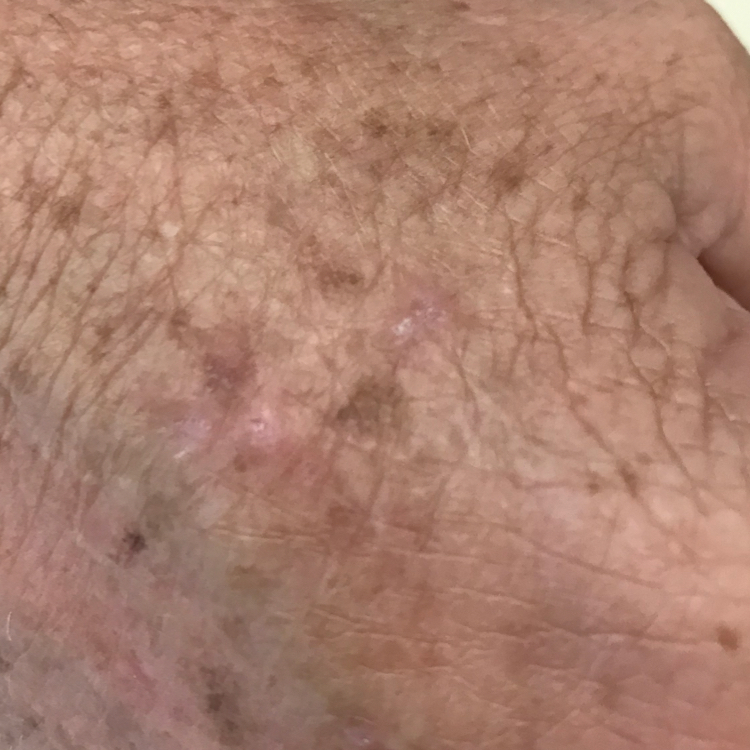Q: What is the imaging modality?
A: clinical photo
Q: Patient demographics?
A: age 48
Q: Where on the body is the lesion?
A: a hand
Q: Any reported symptoms?
A: growth
Q: What was the clinical impression?
A: actinic keratosis (clinical consensus)